The subject is a female aged 30–39. Located on the top or side of the foot. This image was taken at an angle.
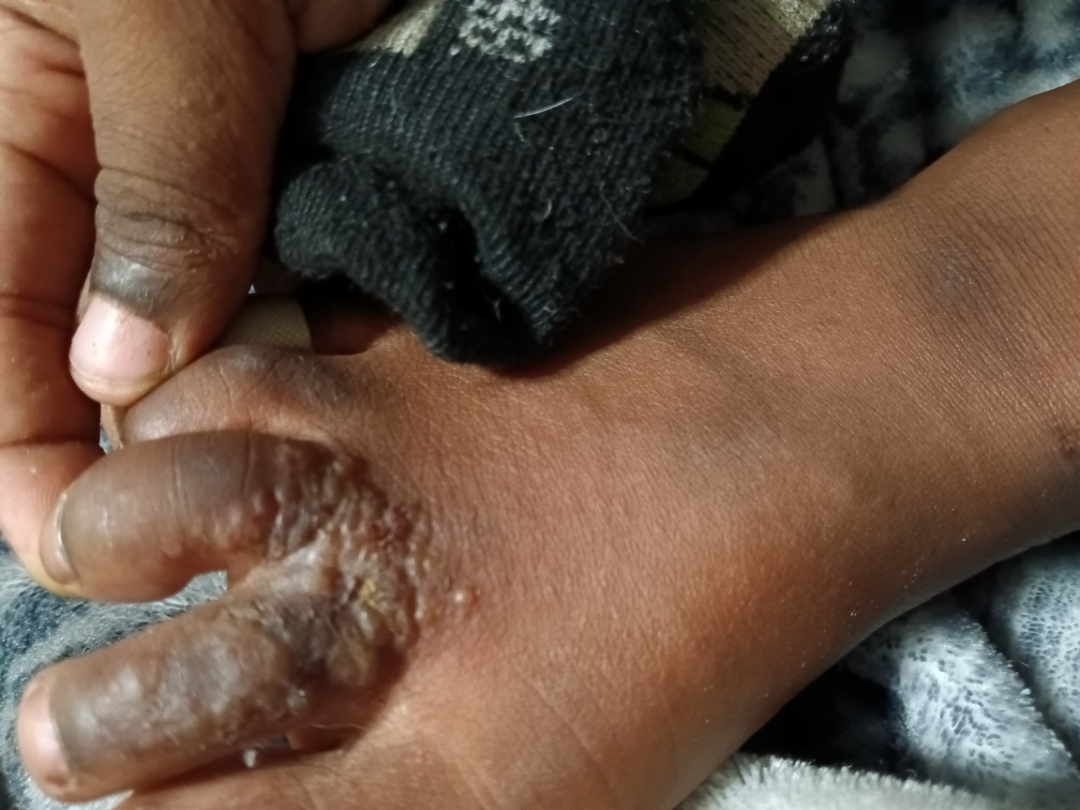Three dermatologists independently reviewed the case: the impression was split between Tinea and Eczema; an alternative is Skin and soft tissue atypical mycobacterial infection; less likely is Allergic Contact Dermatitis.